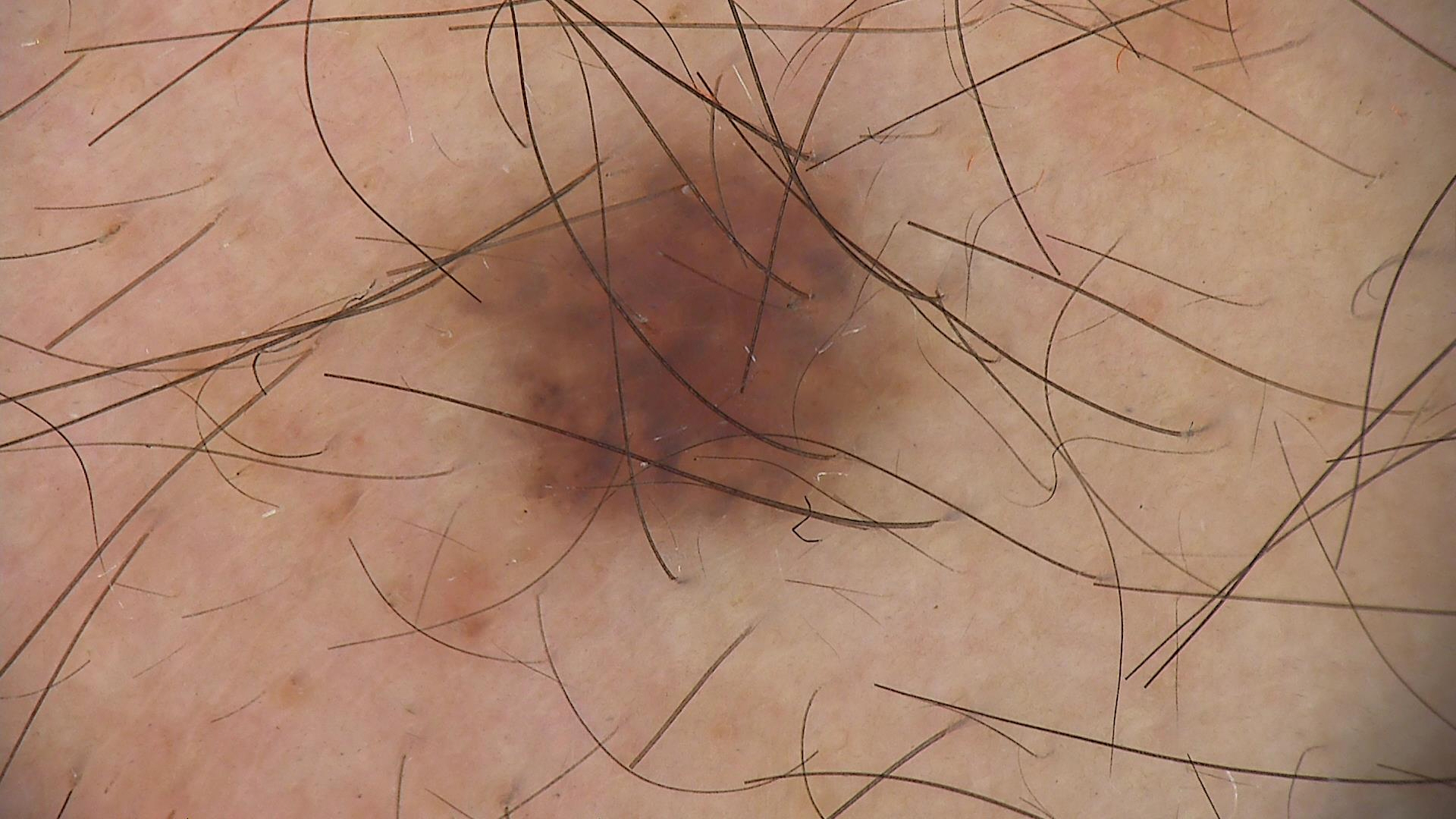Consistent with a dysplastic junctional nevus.